A dermatoscopic image of a skin lesion; the patient is a male approximately 30 years of age.
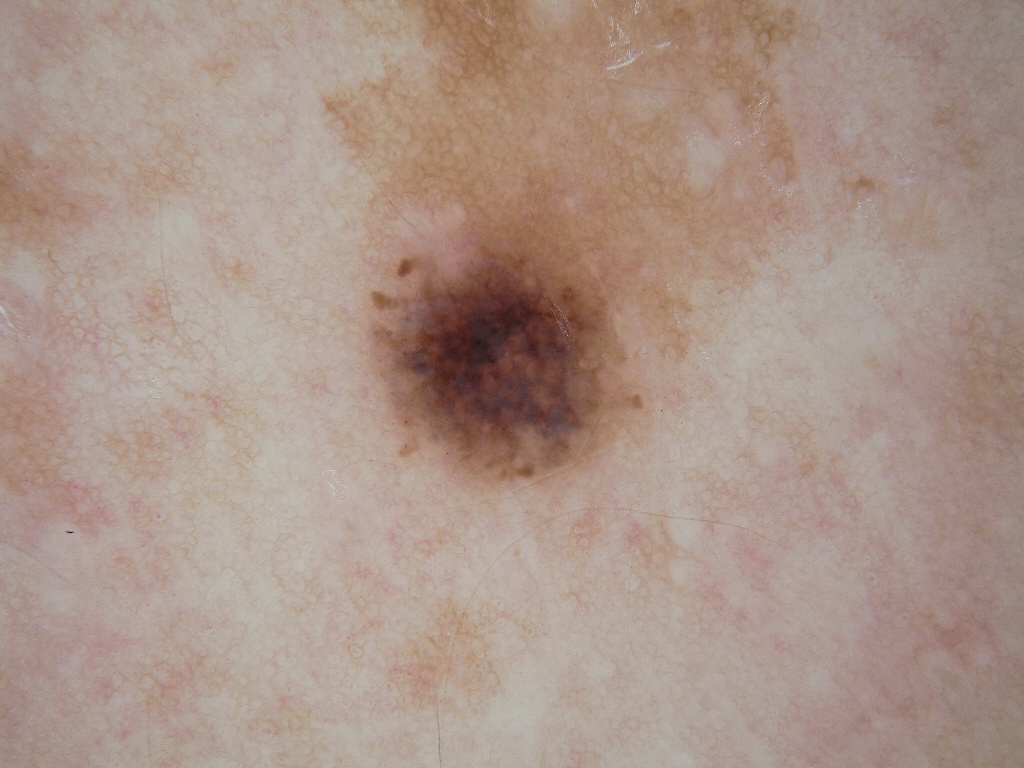Dermoscopic review identifies globules, with no milia-like cysts, negative network, pigment network, or streaks. The lesion's extent is x1=304 y1=4 x2=850 y2=514. The diagnostic assessment was a melanocytic nevus, a benign lesion.